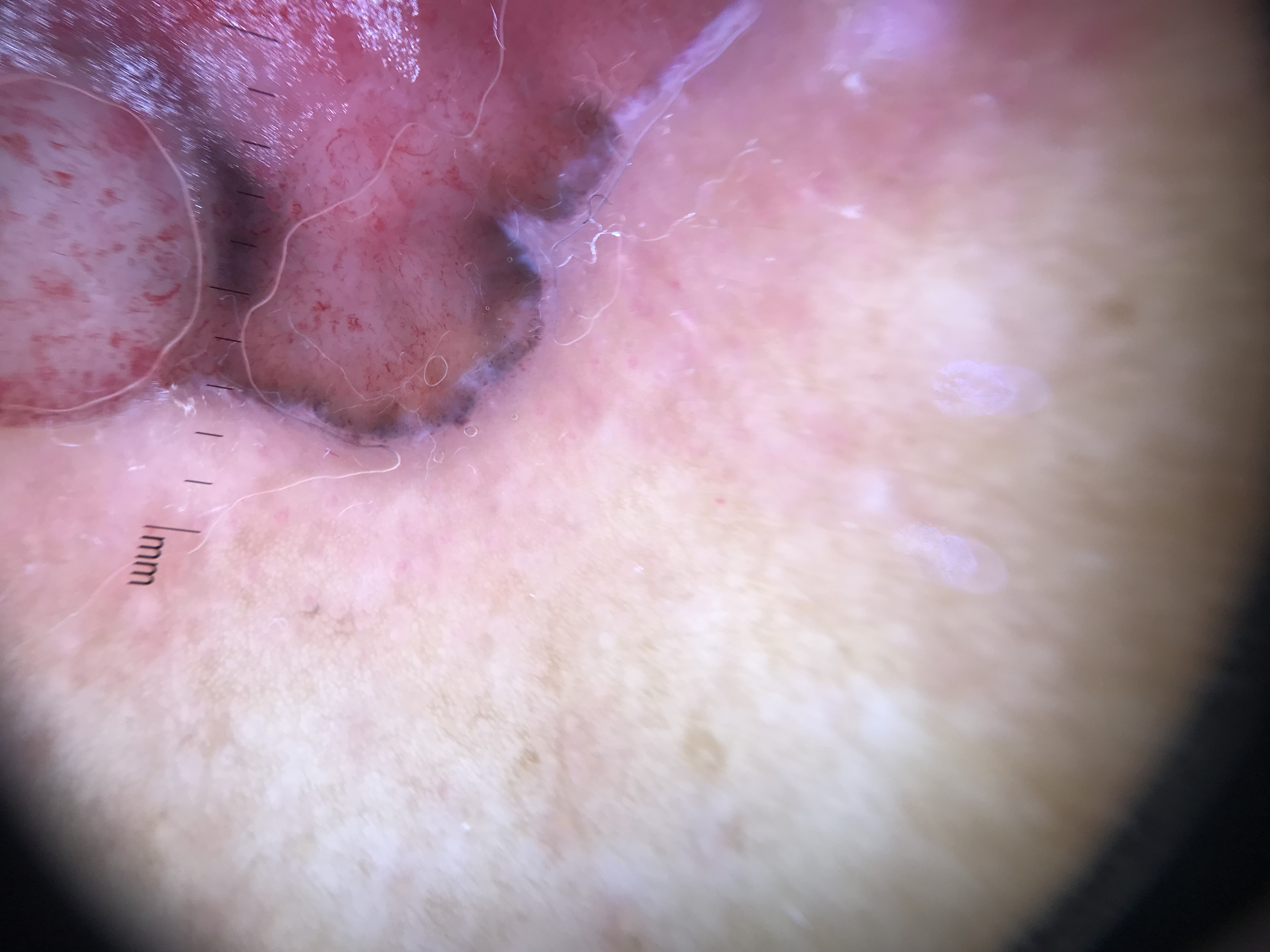Q: What is this lesion?
A: basal cell carcinoma (biopsy-proven)